A dermoscopic photograph of a skin lesion:
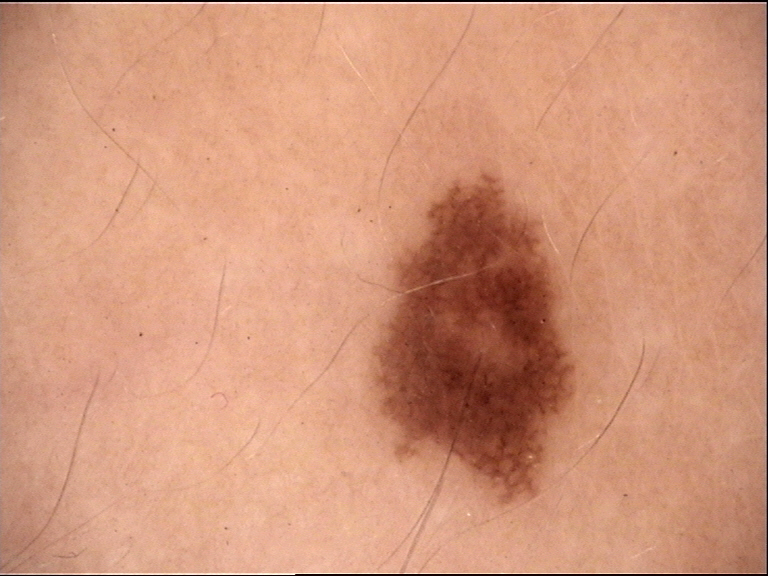{
  "lesion_type": {
    "main_class": "banal",
    "pattern": "junctional"
  },
  "diagnosis": {
    "name": "junctional nevus",
    "code": "jb",
    "malignancy": "benign",
    "super_class": "melanocytic",
    "confirmation": "expert consensus"
  }
}